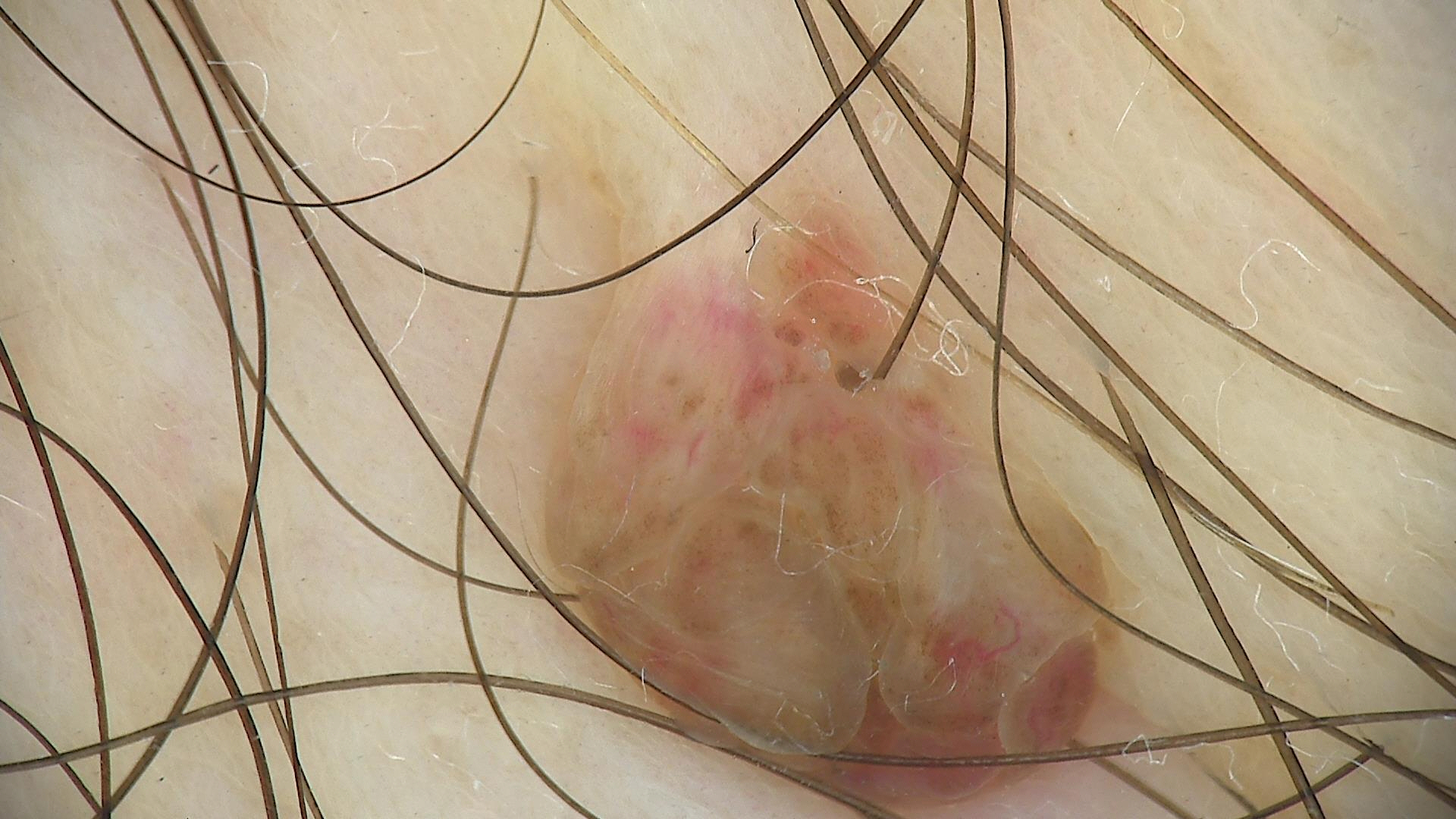Q: What is the imaging modality?
A: dermoscopy
Q: What kind of lesion is this?
A: banal
Q: What is this lesion?
A: dermal nevus (expert consensus)